A dermoscopic close-up of a skin lesion: 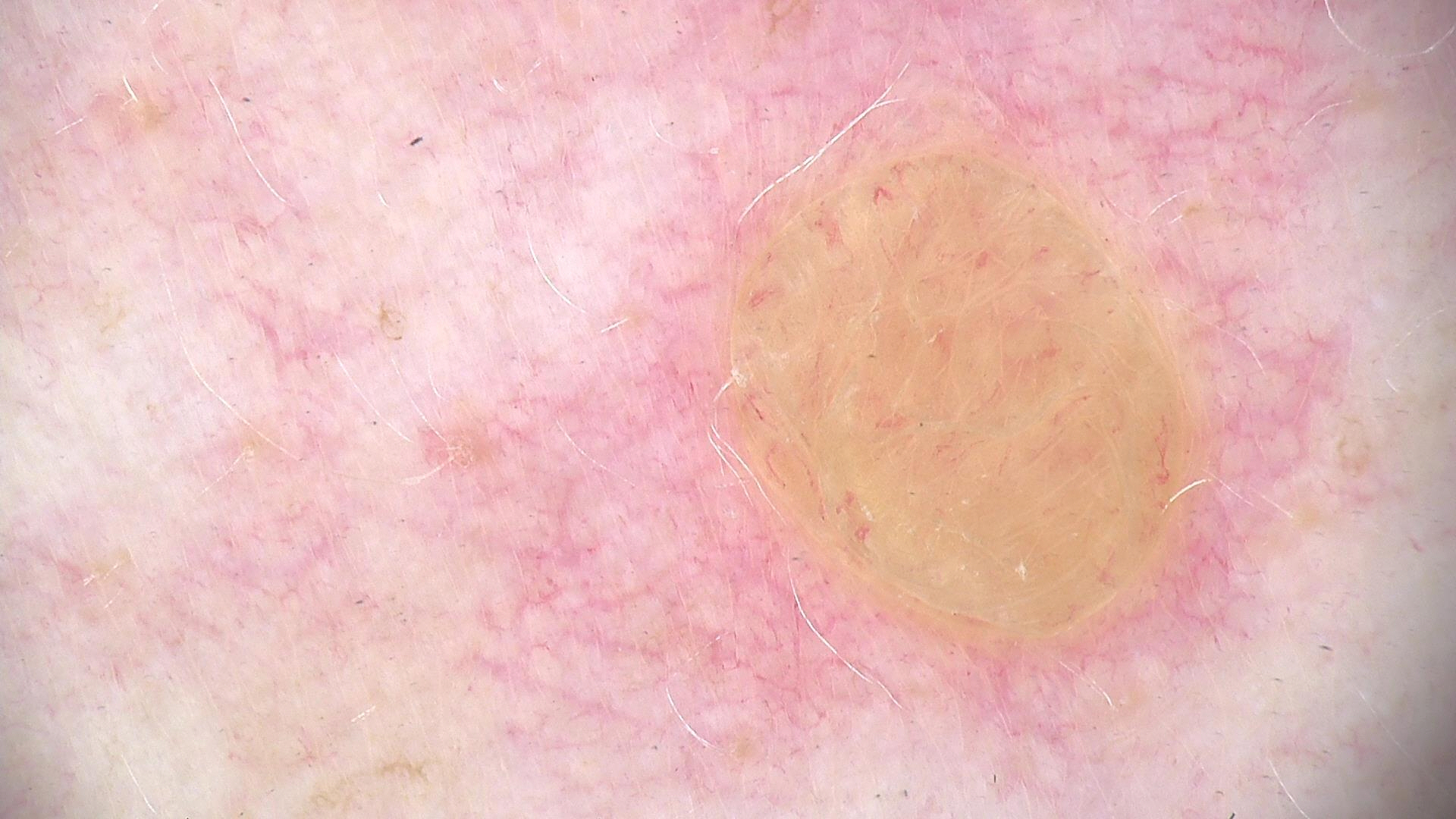Q: How is the lesion classified?
A: banal
Q: What was the diagnostic impression?
A: dermal nevus (expert consensus)